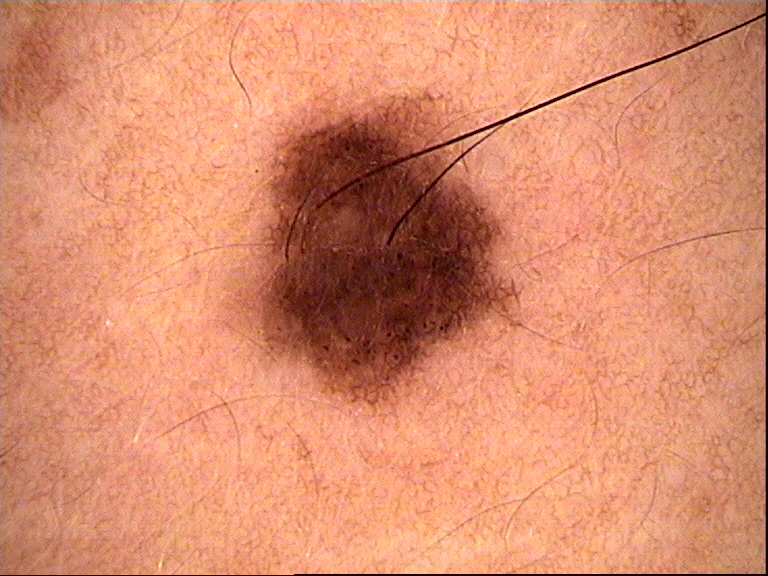label: dysplastic compound nevus (expert consensus).